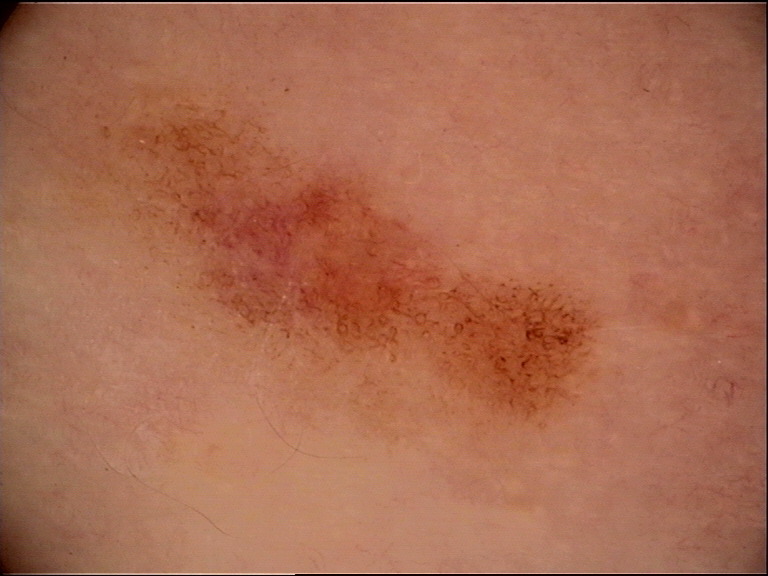Conclusion: Labeled as a dysplastic junctional nevus.